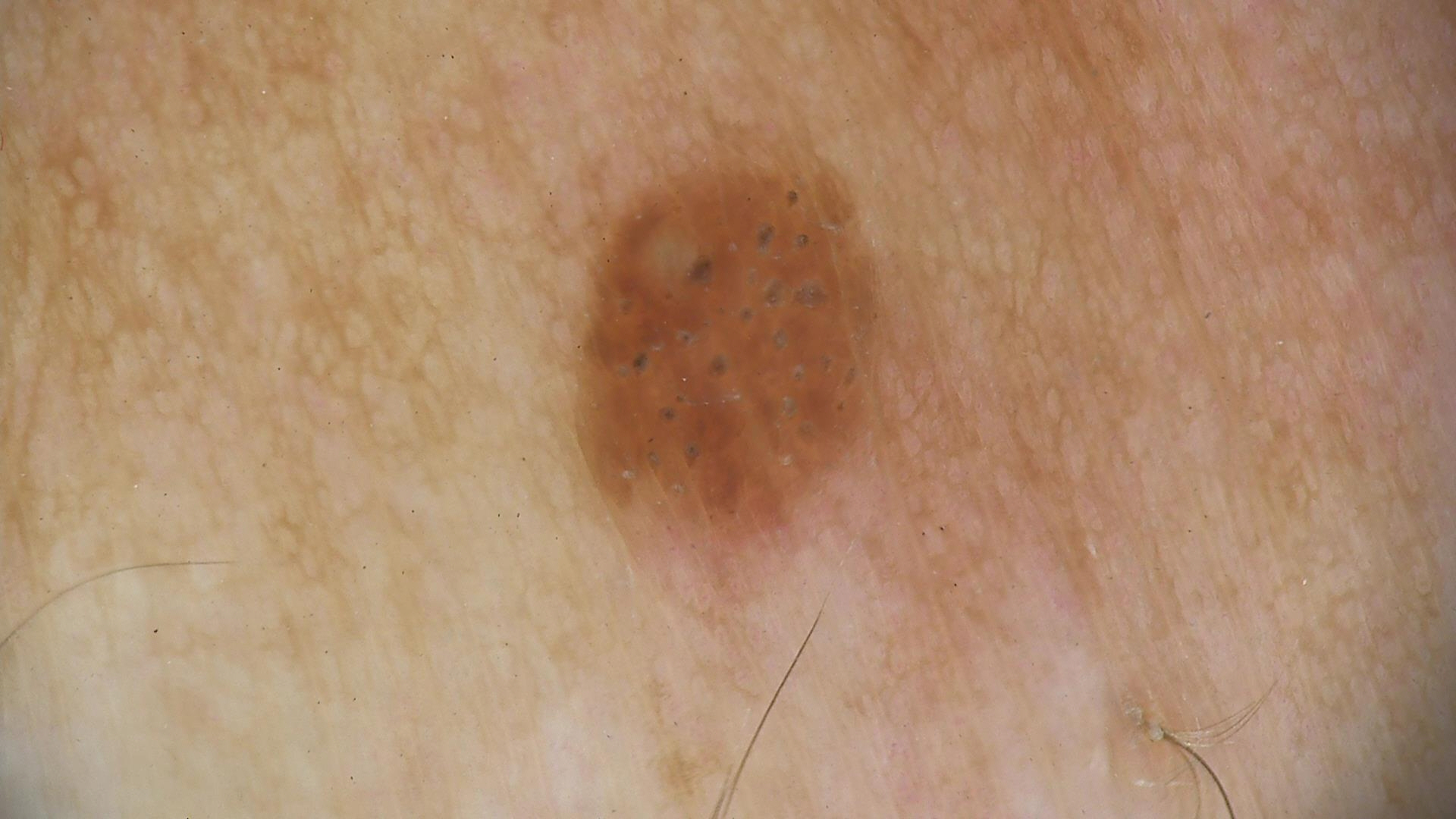| key | value |
|---|---|
| image | dermatoscopy |
| assessment | seborrheic keratosis (expert consensus) |